The lesion involves the leg, the photograph is a close-up of the affected area, the contributor notes the condition has been present for one to four weeks, texture is reported as rough or flaky, the patient considered this a rash, skin tone: Fitzpatrick skin type III: 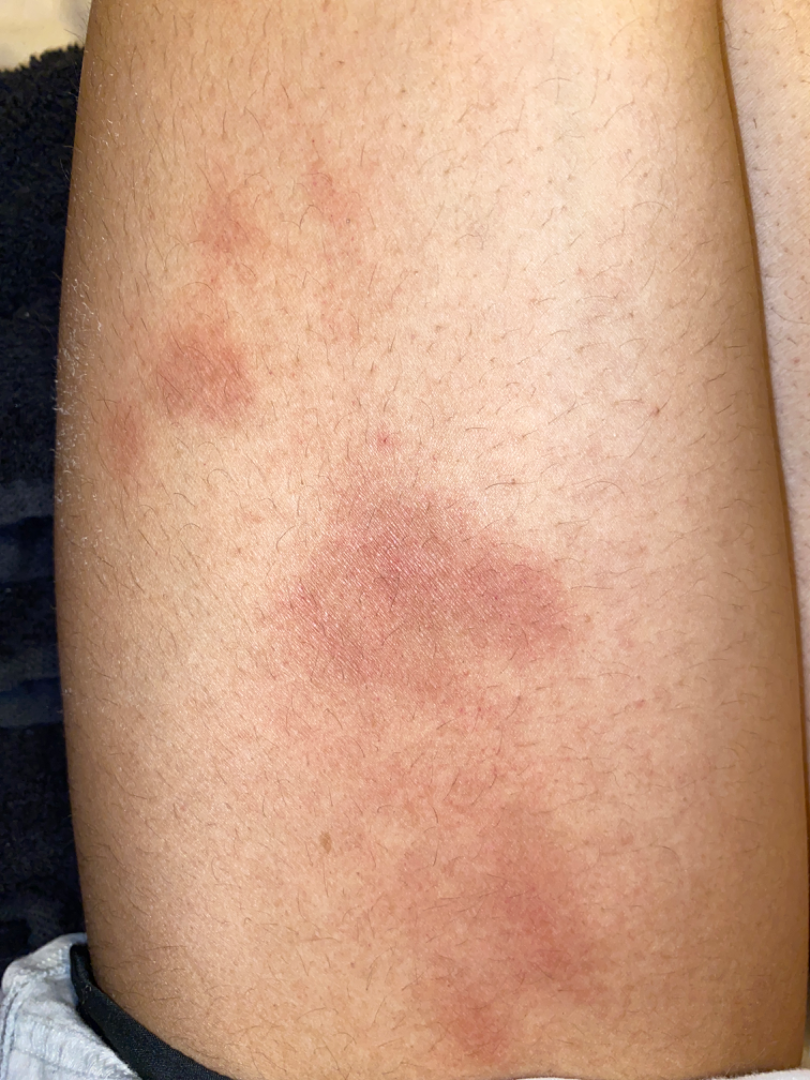On photographic review, Kaposi's sarcoma of skin (0.41); ecchymoses (0.41); resolving dermatitis (0.18).